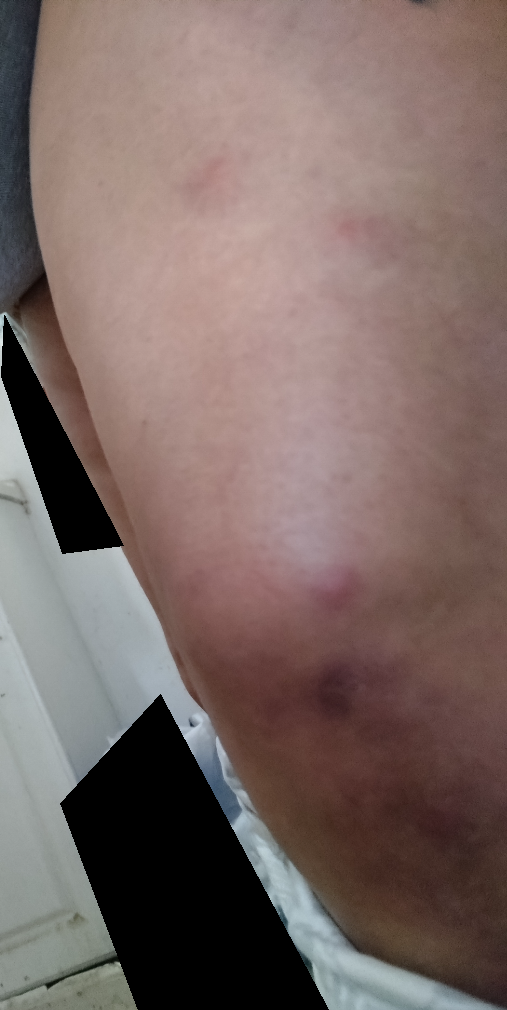The reviewing dermatologist was unable to assign a differential diagnosis from the image.
An image taken at a distance.